Reported lesion symptoms include itching · the photograph is a close-up of the affected area · Fitzpatrick phototype III; lay reviewers estimated Monk Skin Tone 3 or 4 · the head or neck is involved · the patient indicates the lesion is raised or bumpy · the patient considered this a rash: 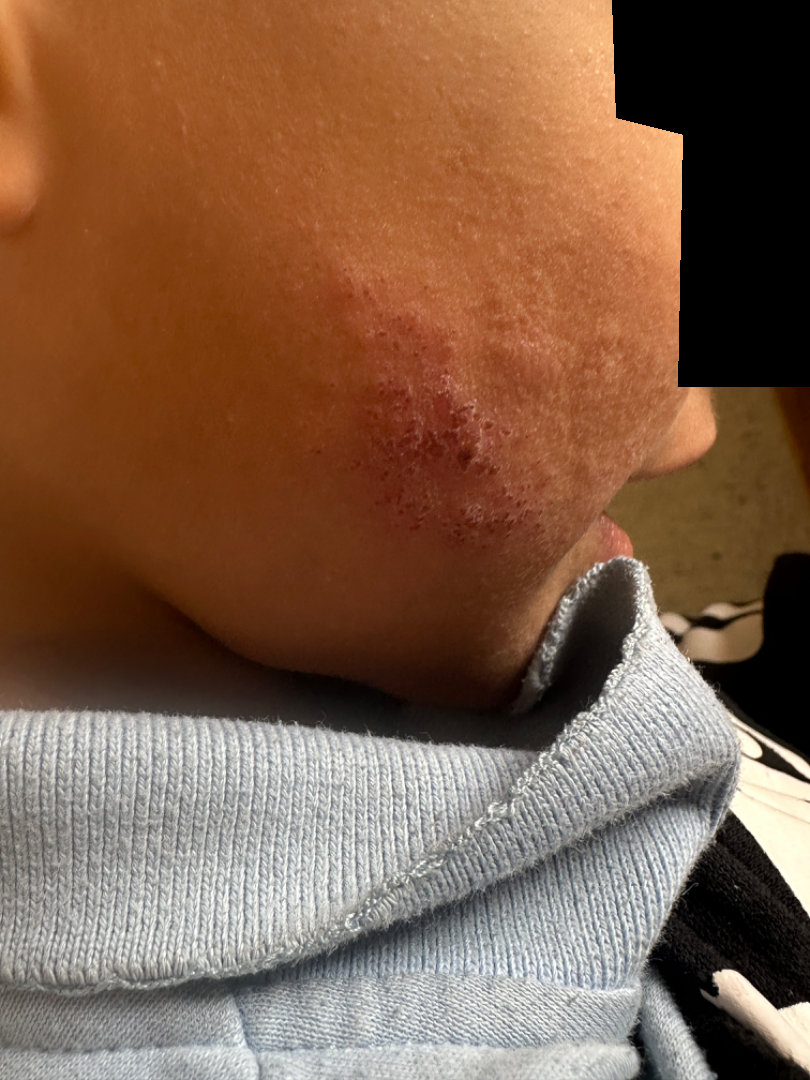Q: What is the dermatologist's impression?
A: the leading consideration is Impetigo